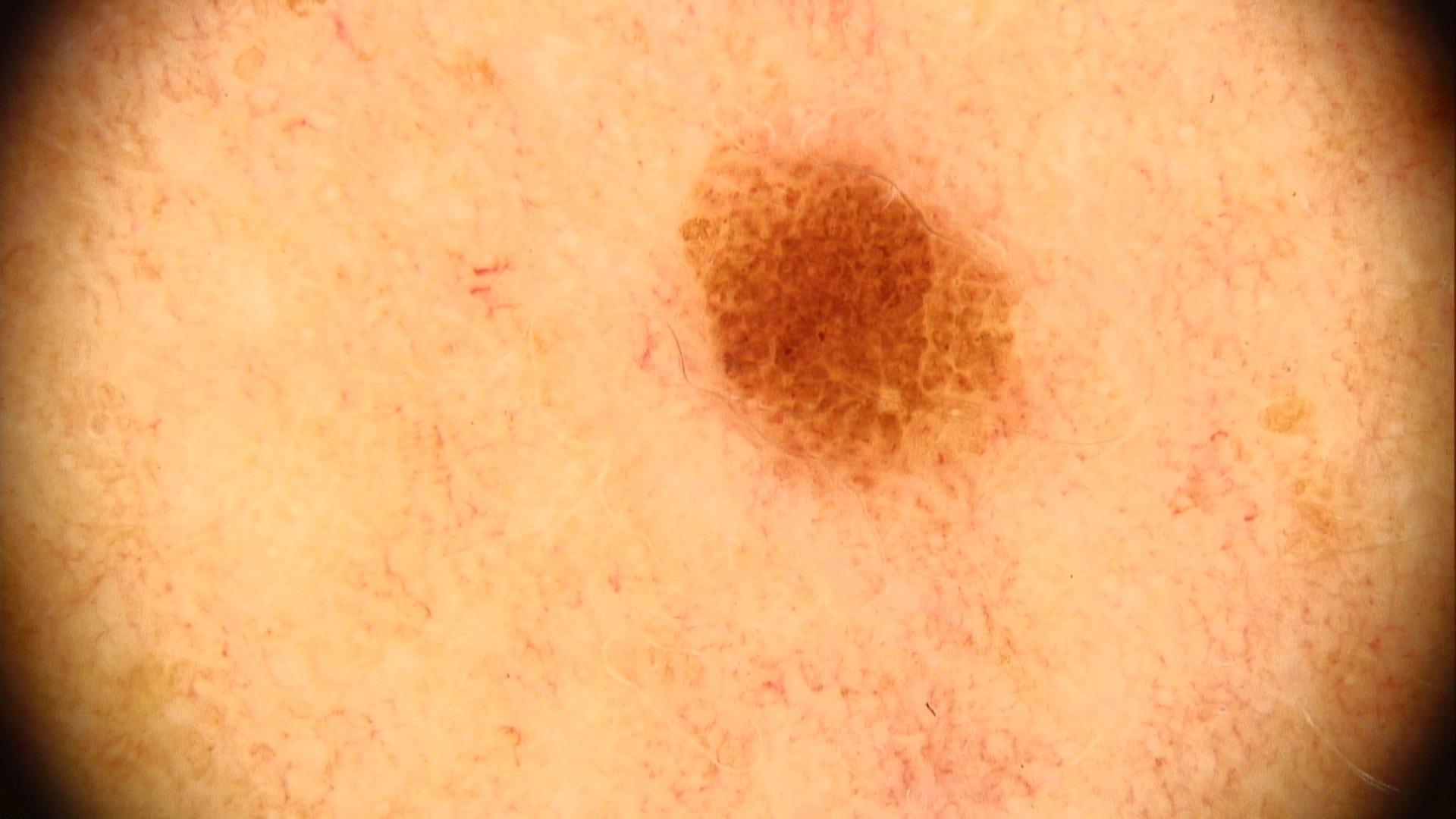A male subject aged 38-42. The chart notes a first-degree relative with melanoma. A dermatoscopic image of a skin lesion. FST III. The lesion is on the head or neck. Expert review favored a benign lesion — a nevus.